No constitutional symptoms were reported; reported duration is less than one week; the contributor is 30–39, male; the contributor reports the lesion is fluid-filled and raised or bumpy; skin tone: FST II; the photograph was taken at a distance; the lesion is associated with bothersome appearance and enlargement:
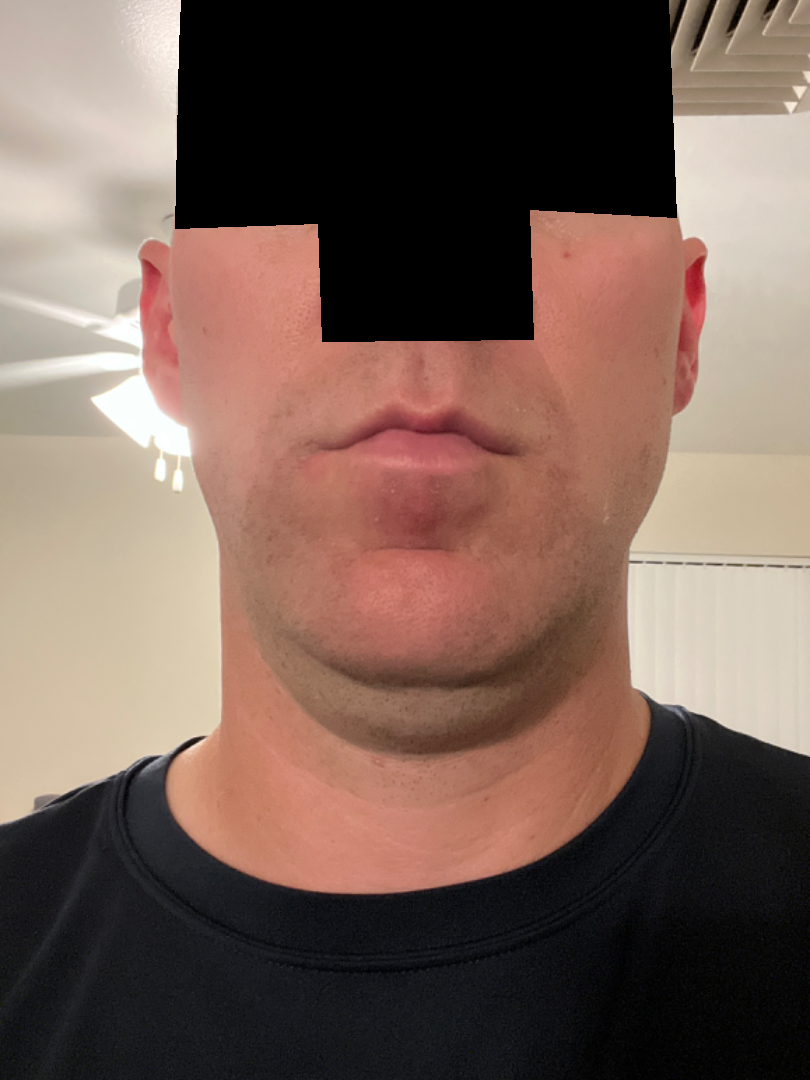The reviewing dermatologist's impression was: consistent with Irritant Contact Dermatitis.